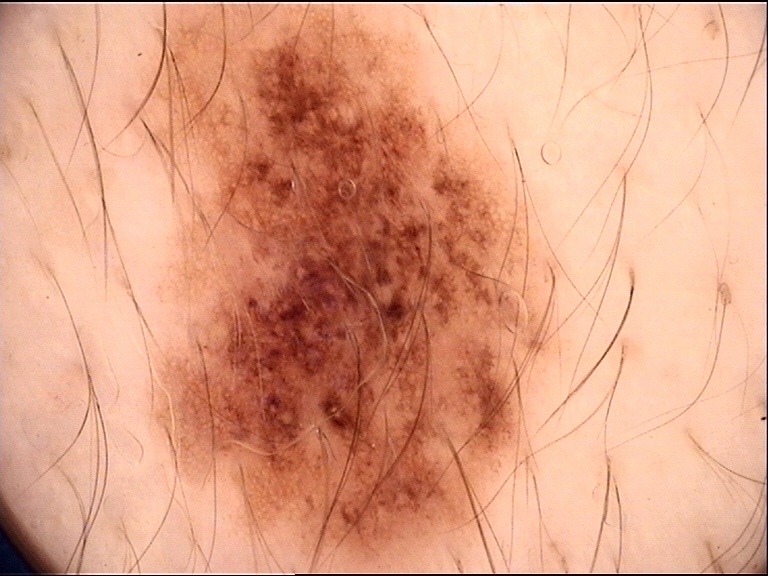Summary:
A skin lesion imaged with a dermatoscope.
Conclusion:
Diagnosed as a dysplastic junctional nevus.